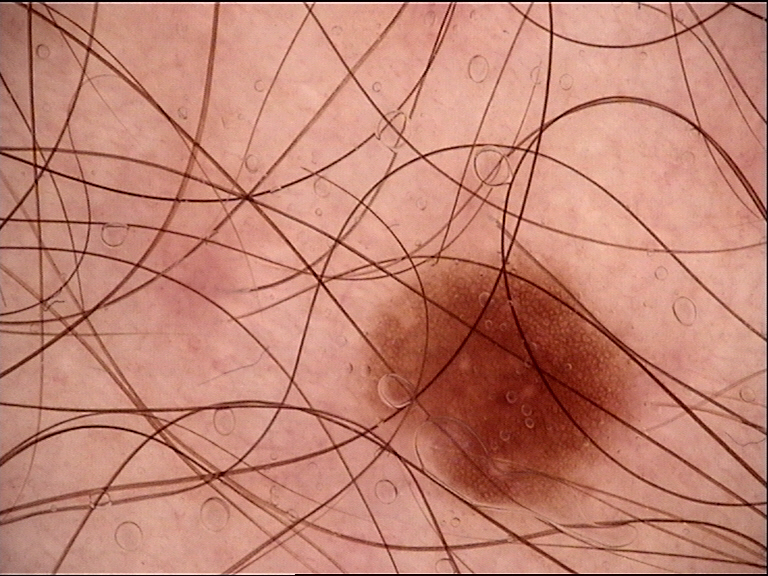image type: dermatoscopy; label: dysplastic junctional nevus (expert consensus).